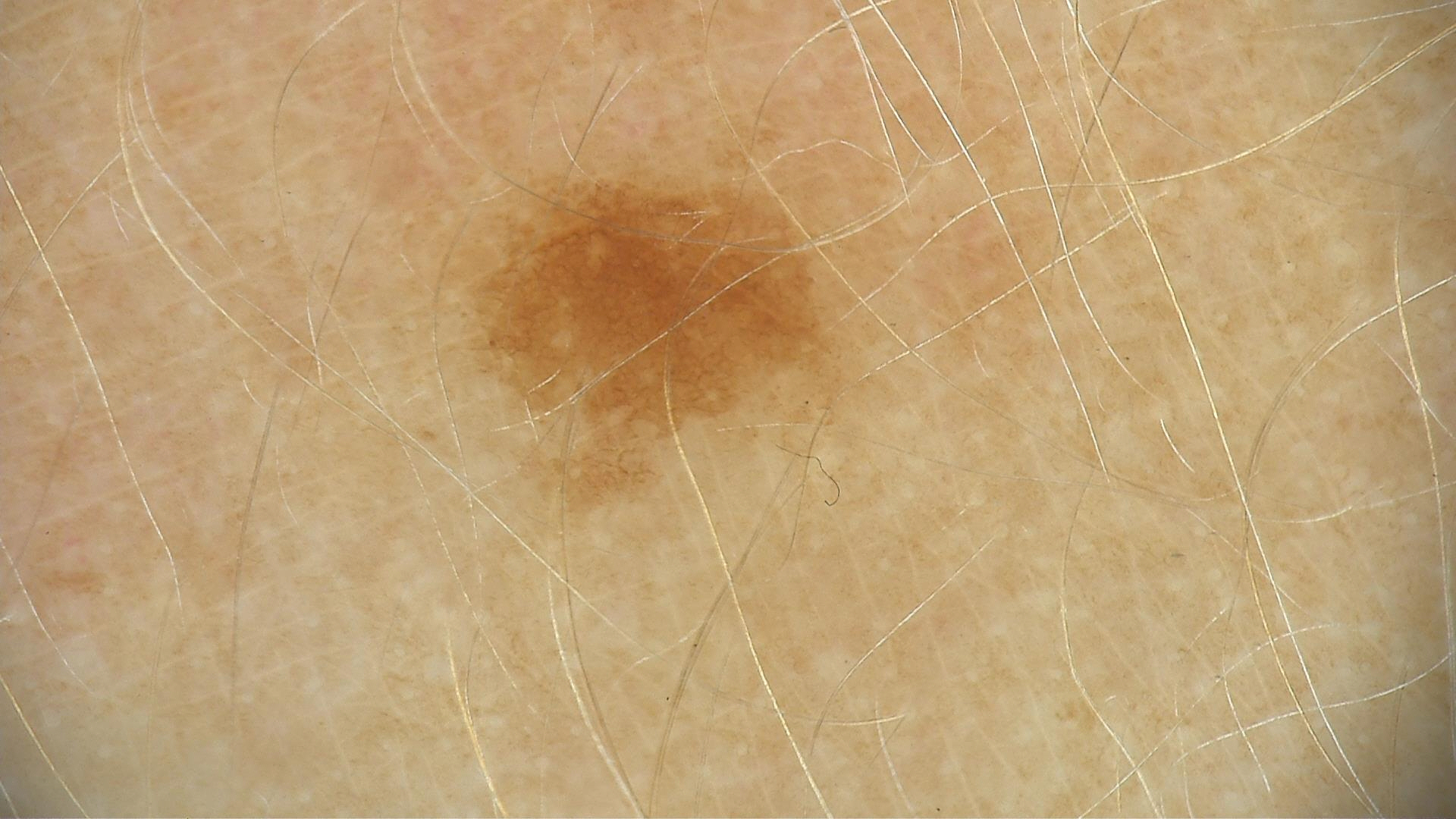assessment = dysplastic junctional nevus (expert consensus).